A dermoscopic close-up of a skin lesion: 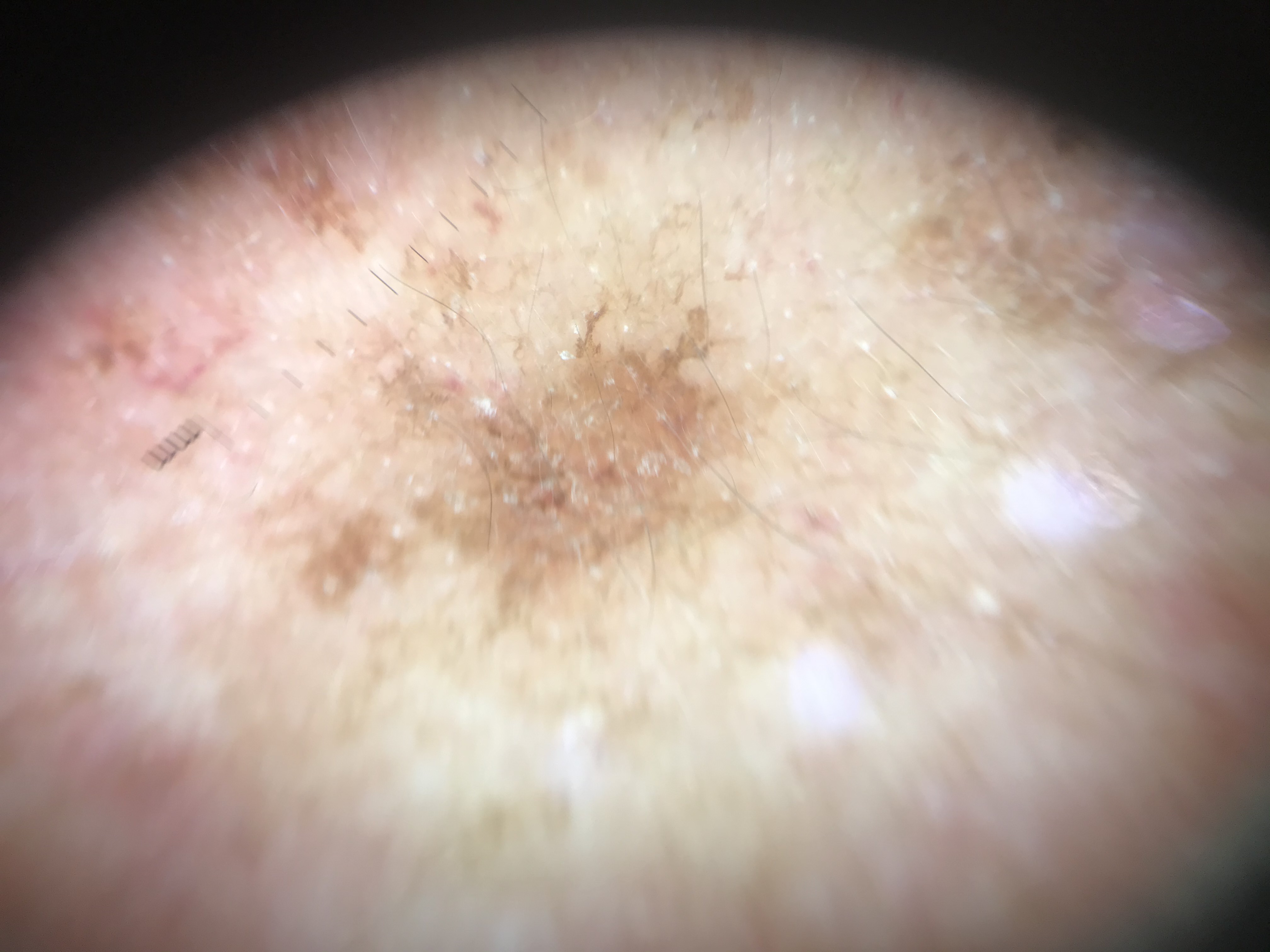<lesion>
  <lesion_type>
    <main_class>keratinocytic</main_class>
  </lesion_type>
  <diagnosis>
    <name>actinic keratosis</name>
    <code>ak</code>
    <malignancy>indeterminate</malignancy>
    <super_class>non-melanocytic</super_class>
    <confirmation>expert consensus</confirmation>
  </diagnosis>
</lesion>